The back of the hand, back of the torso, front of the torso and arm are involved. Close-up view. No relevant systemic symptoms. Self-categorized by the patient as a rash:
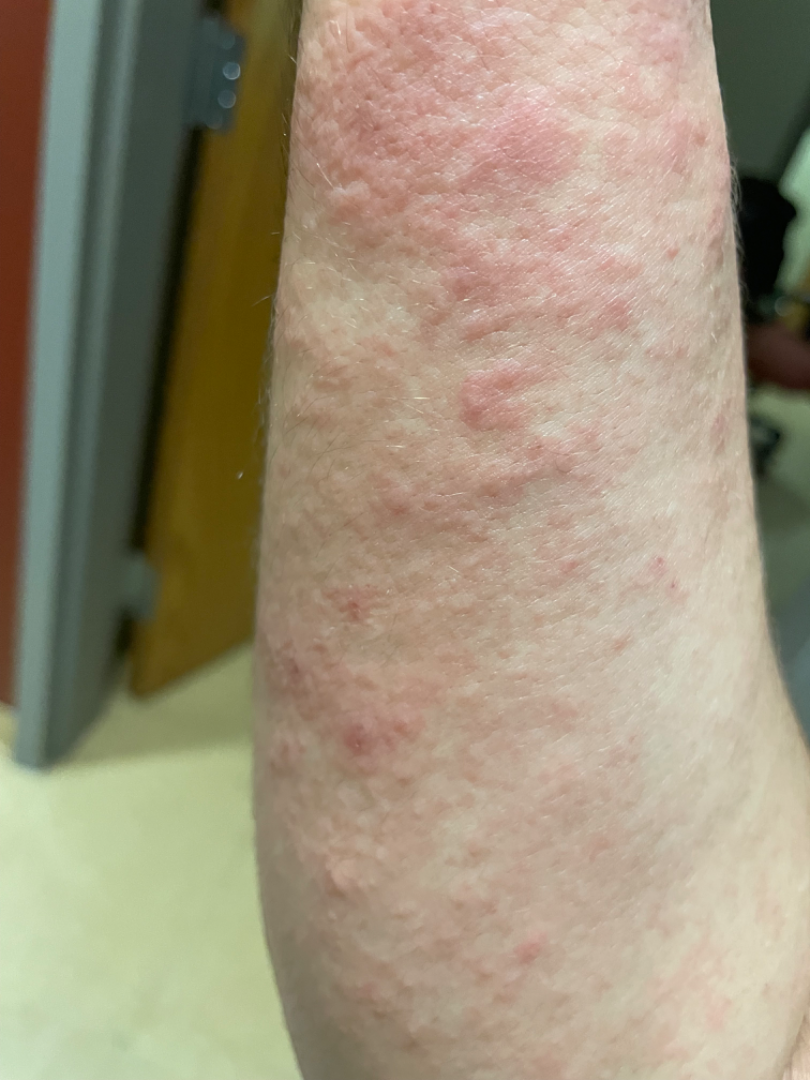Impression: The differential is split between Eczema and Acute dermatitis, NOS.